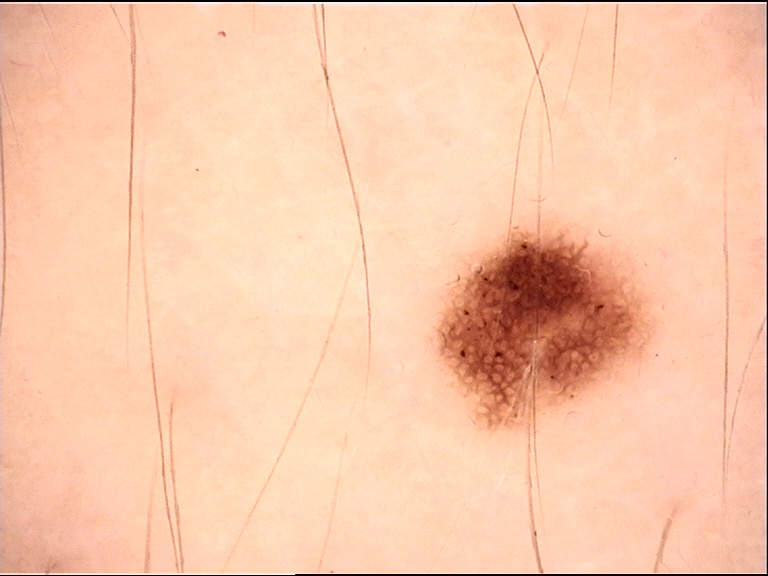Q: What is this lesion?
A: dysplastic junctional nevus (expert consensus)